A dermoscopy image of a single skin lesion: 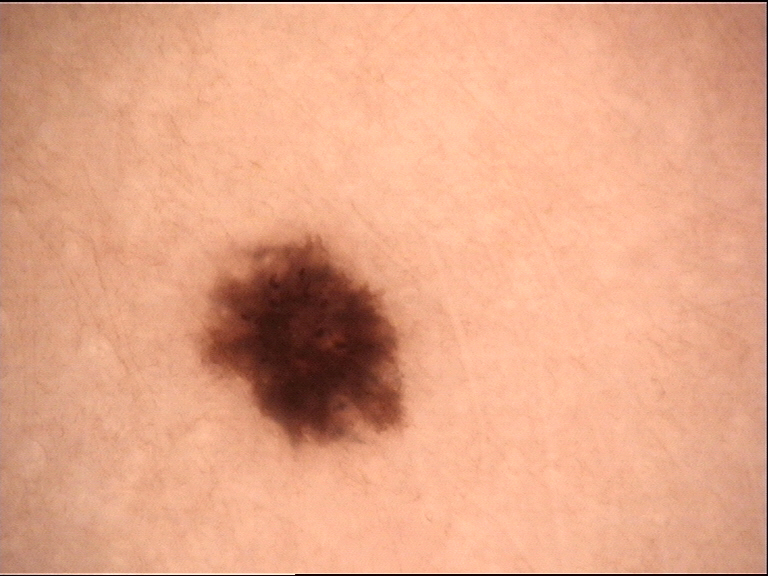assessment = dysplastic junctional nevus (expert consensus)